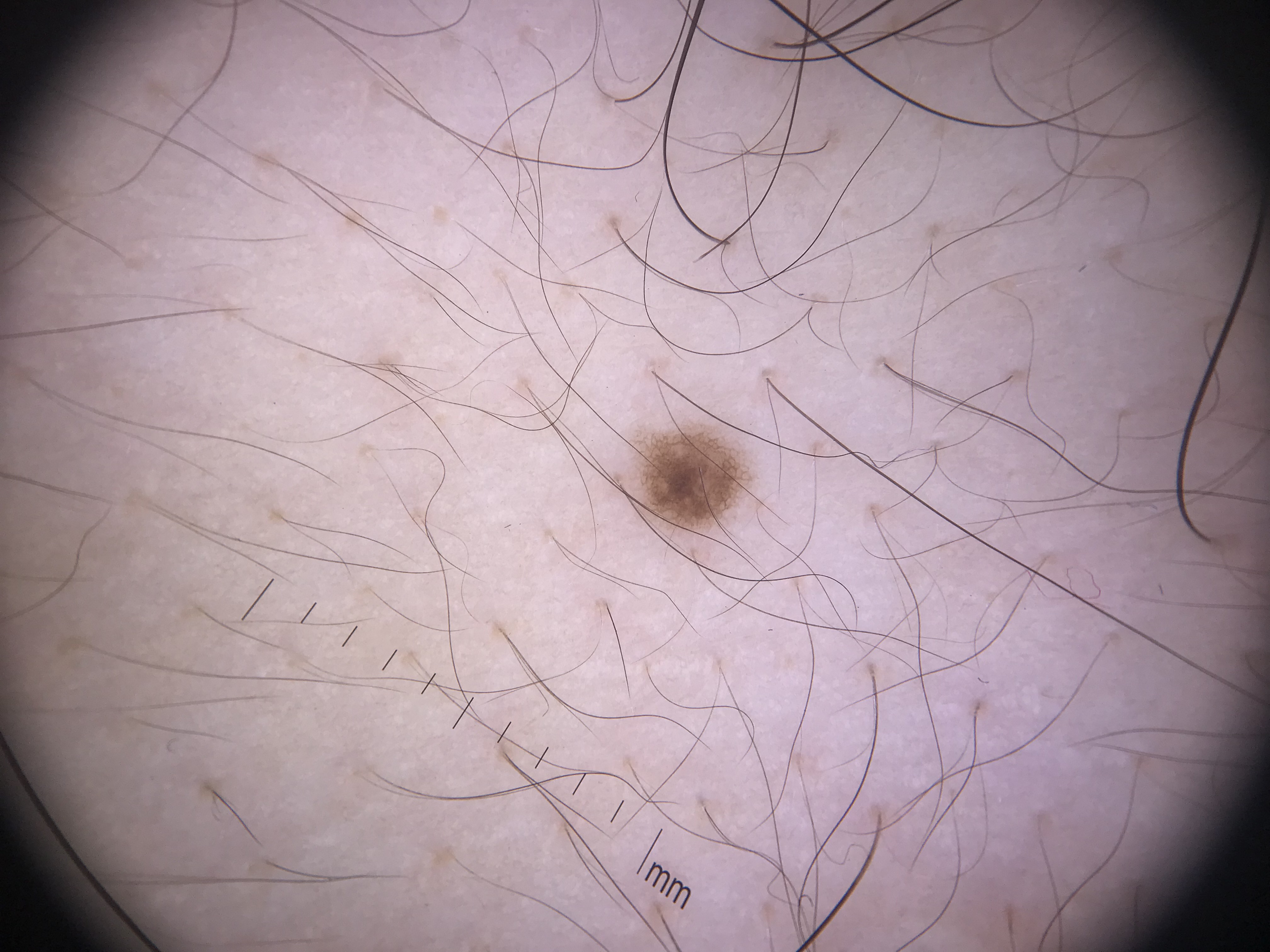Summary: Dermoscopy of a skin lesion. This is a banal lesion. Conclusion: Classified as a junctional nevus.